A skin lesion imaged with a dermatoscope.
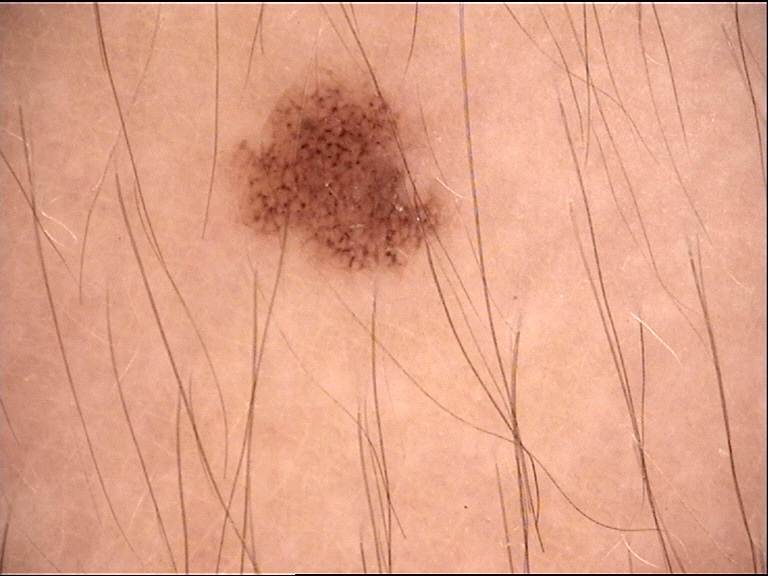diagnosis — dysplastic junctional nevus (expert consensus).